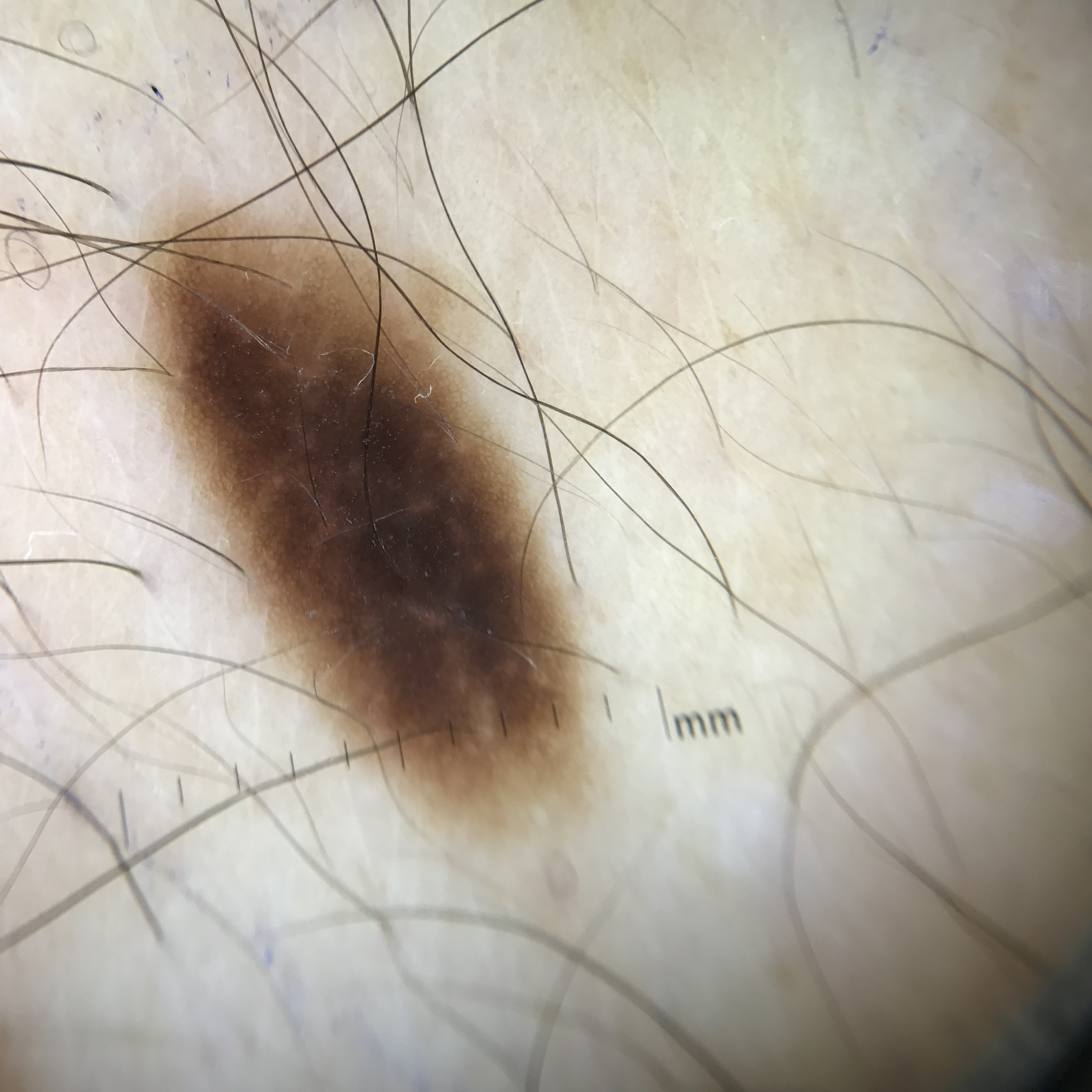Consistent with a benign lesion — a dysplastic junctional nevus.